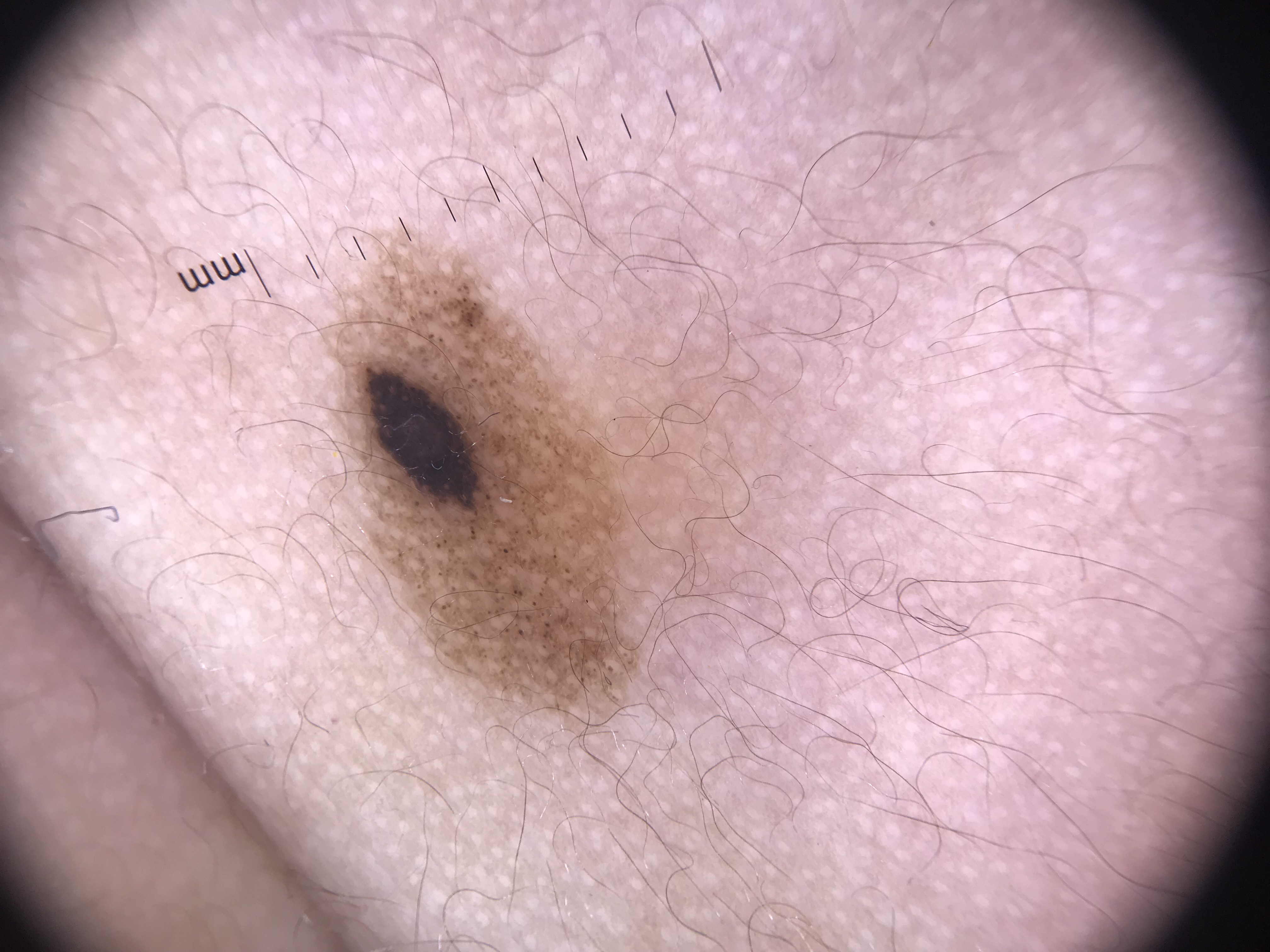| field | value |
|---|---|
| image | dermatoscopy |
| class | congenital compound nevus (expert consensus) |